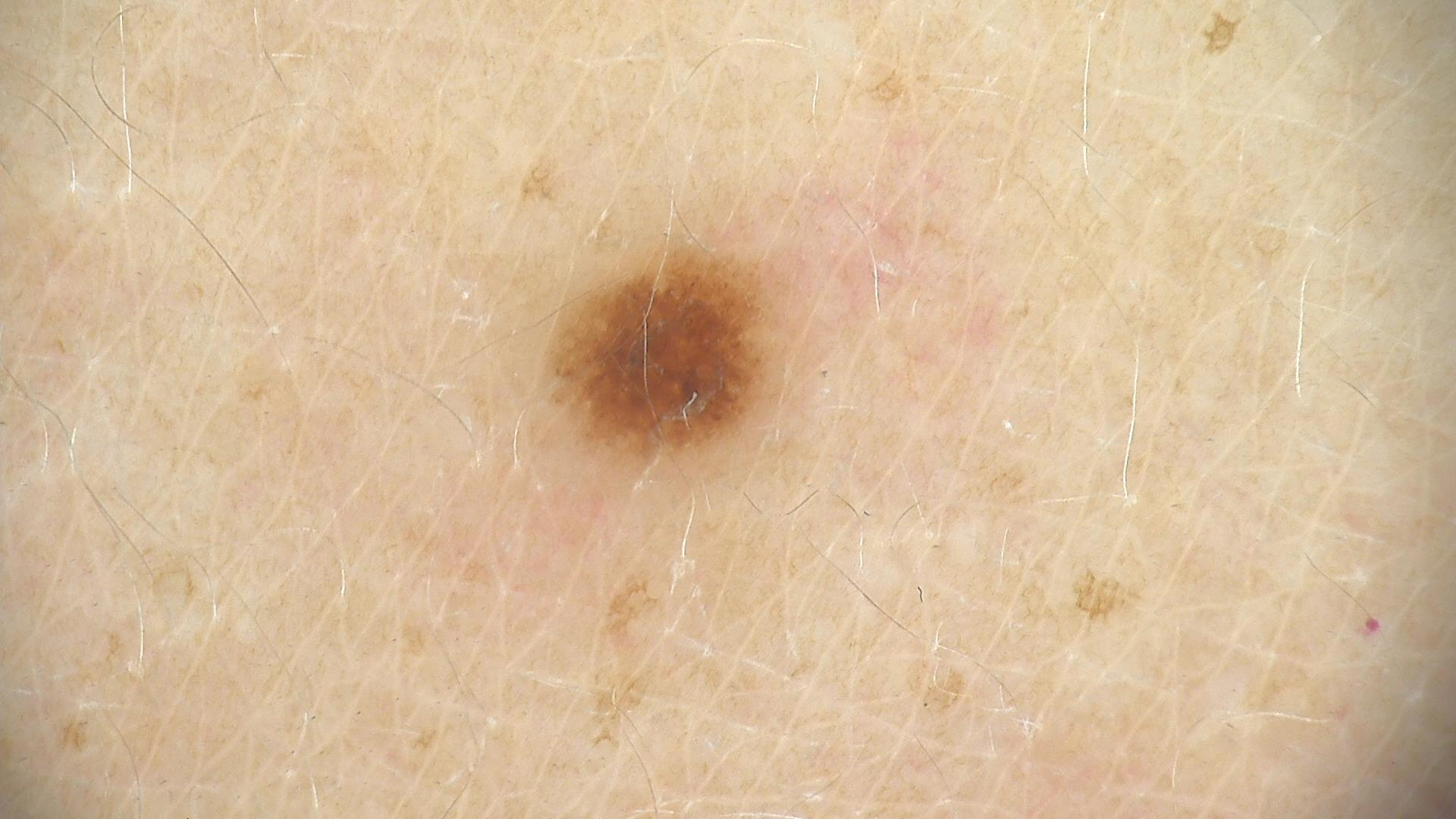A dermoscopic close-up of a skin lesion. Diagnosed as a banal lesion — a junctional nevus.